A close-up photograph; reported duration is one to four weeks; the lesion involves the front of the torso, arm, leg and back of the torso; symptoms reported: bothersome appearance.
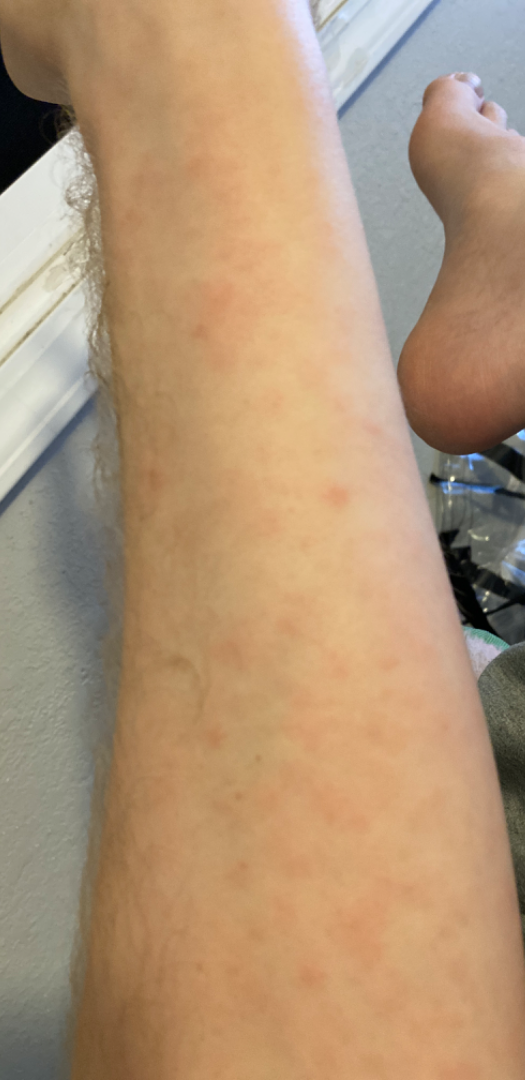Diagnostic features were not clearly distinguishable in this photograph.